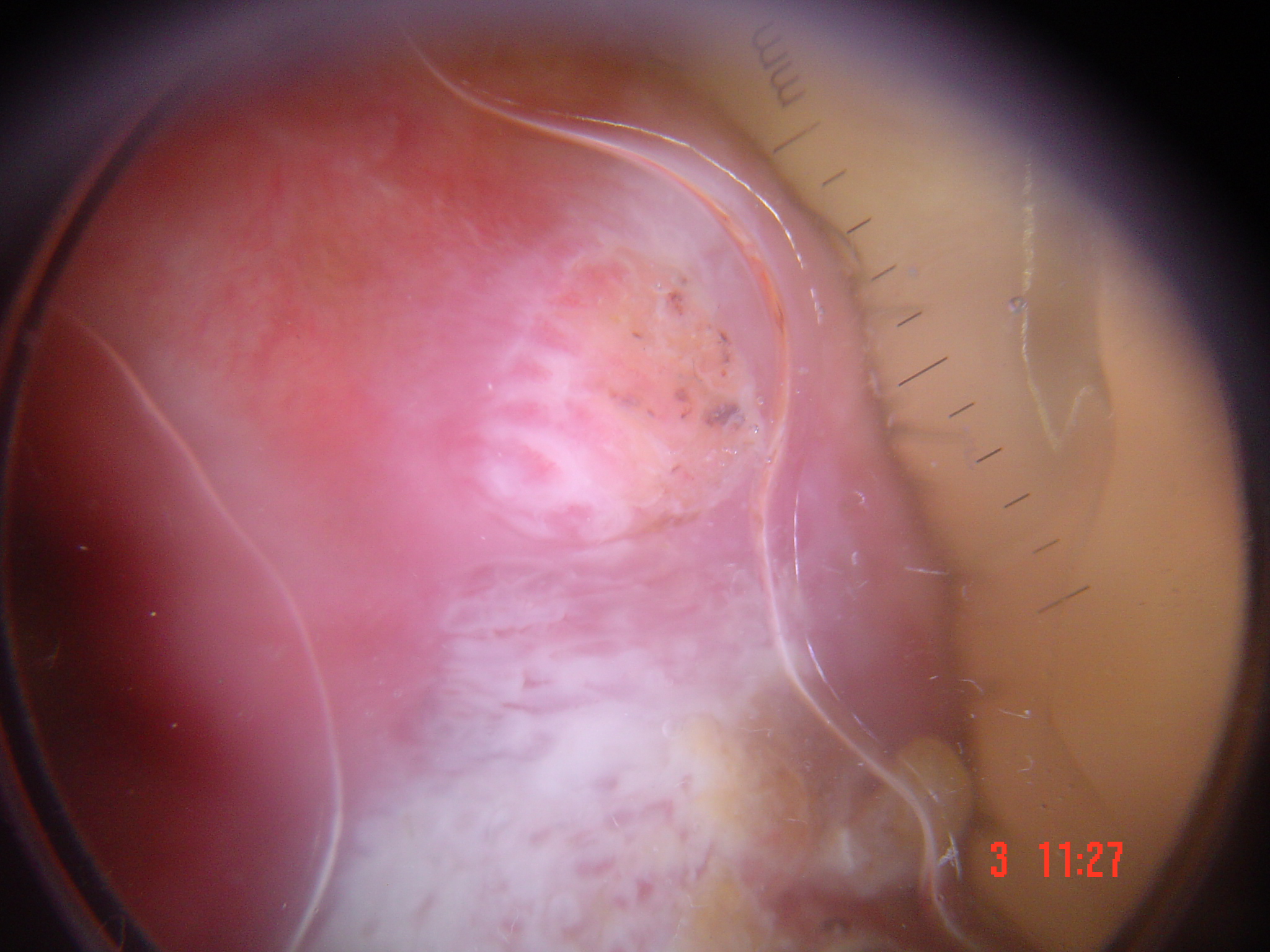lesion type = keratinocytic
diagnostic label = squamous cell carcinoma (biopsy-proven)